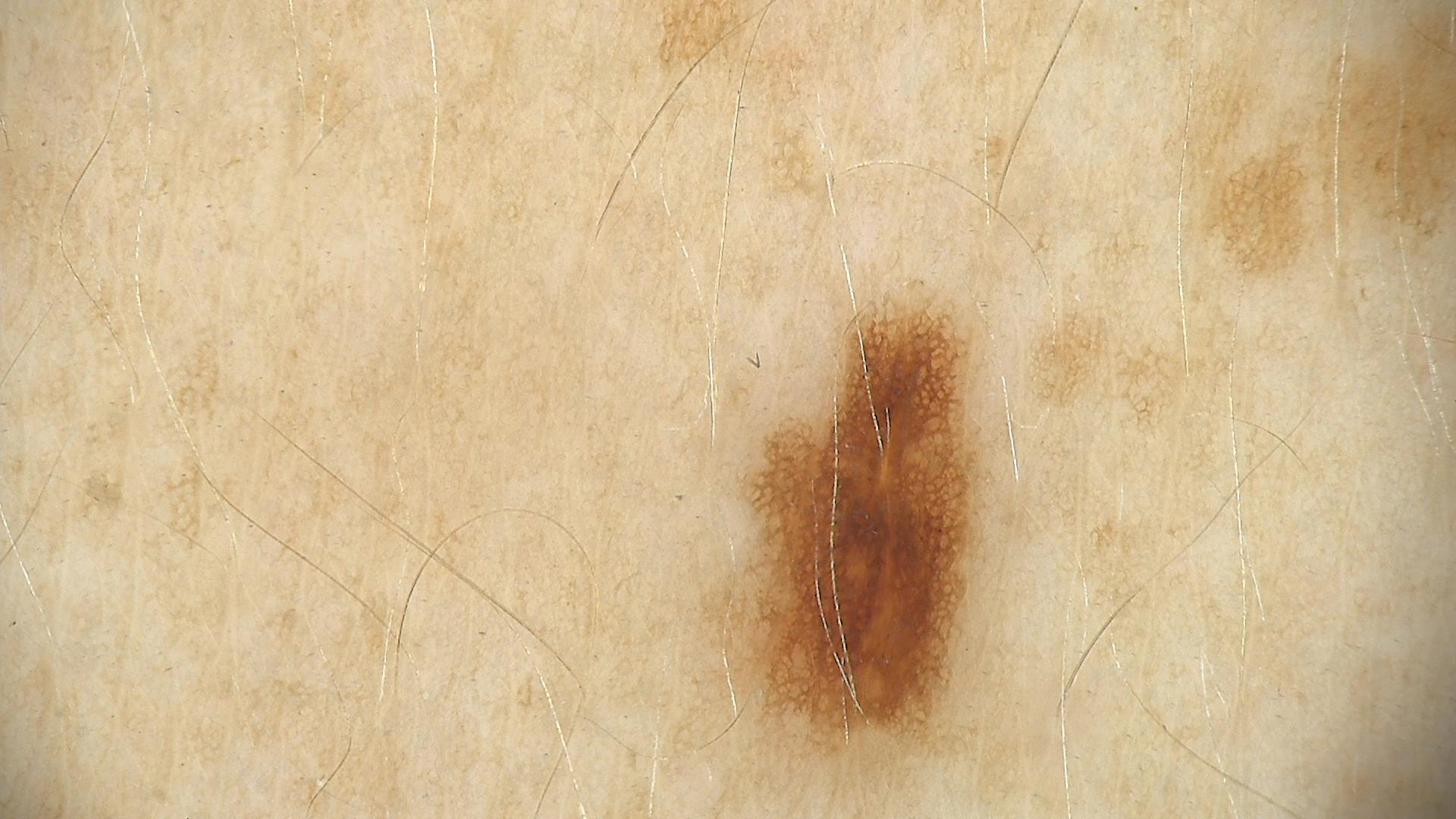The diagnostic label was a dysplastic junctional nevus.